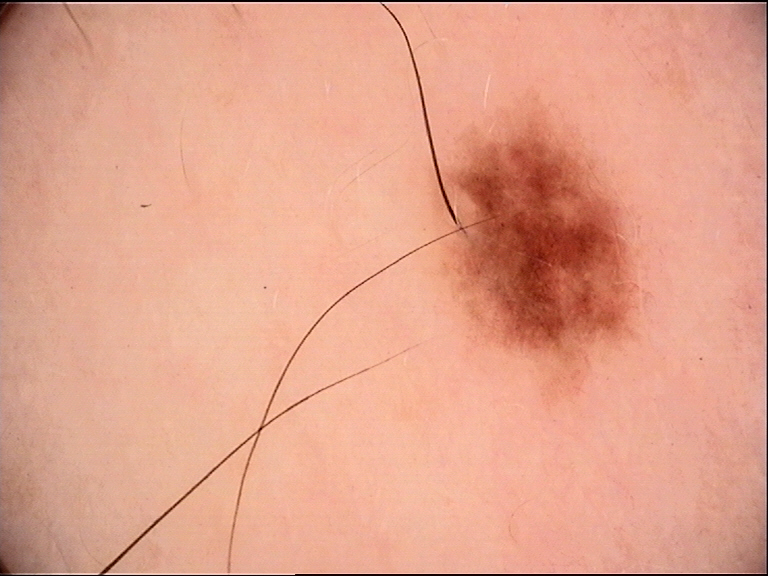Dermoscopy of a skin lesion. The diagnosis was a dysplastic junctional nevus.